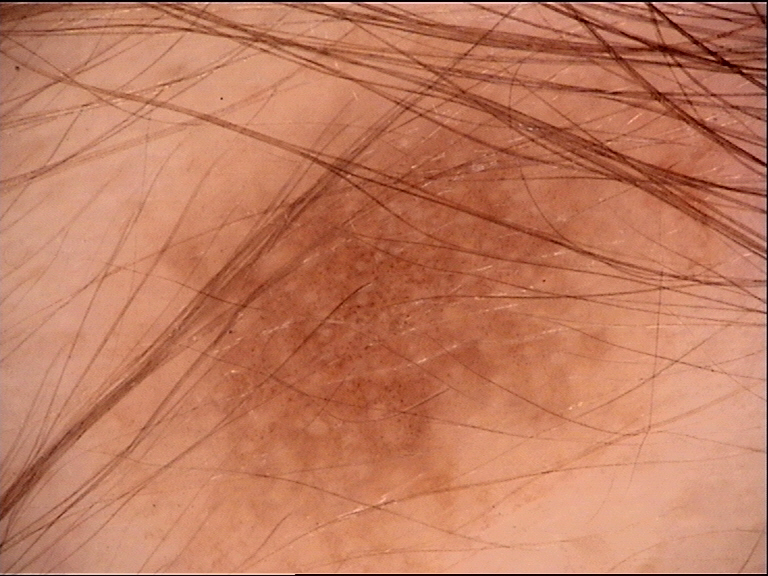image = dermoscopy
lesion type = banal
diagnosis = junctional nevus (expert consensus)